Contact-polarized dermoscopy of a skin lesion. A male subject aged approximately 25.
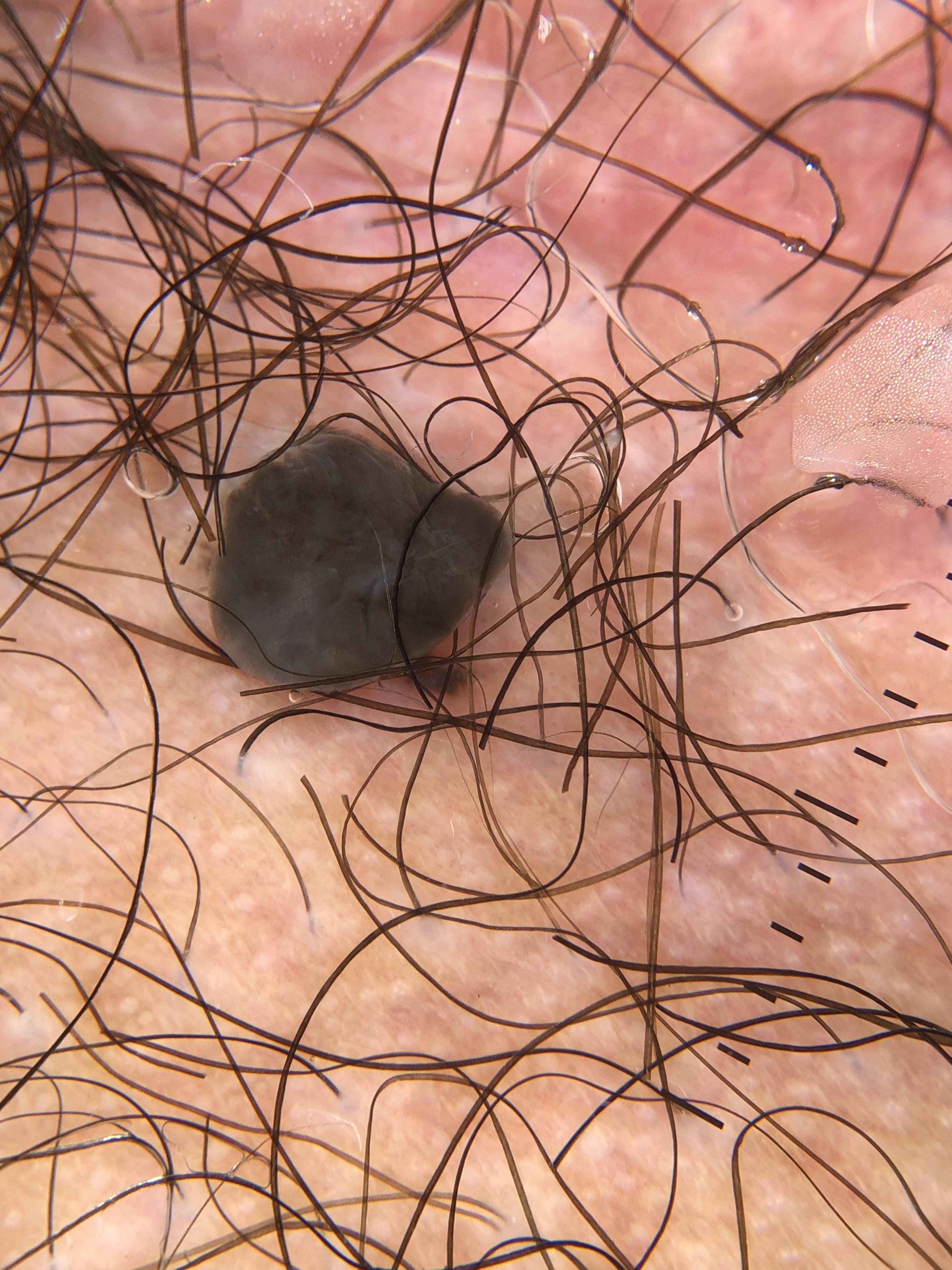The lesion was found on a lower extremity. Confirmed on histopathology as a nevus.